The patient says their skin tans without first burning · few moles overall by the patient's own estimate · imaged for a research study, with no referral diagnosis recorded · a clinical close-up of a skin lesion.
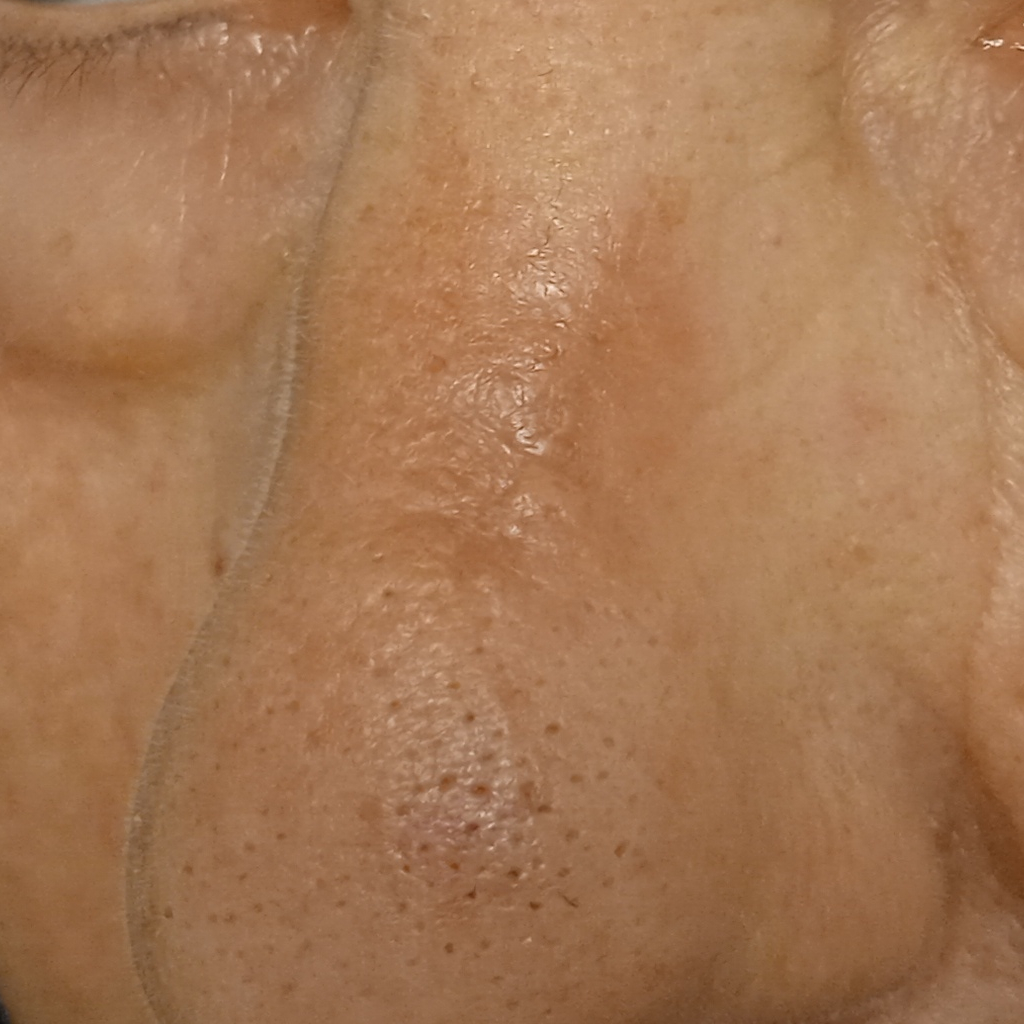Case summary:
The lesion is located on the face. Measuring roughly 9.9 mm.
Conclusion:
Dermatologist review favored an actinic keratosis.